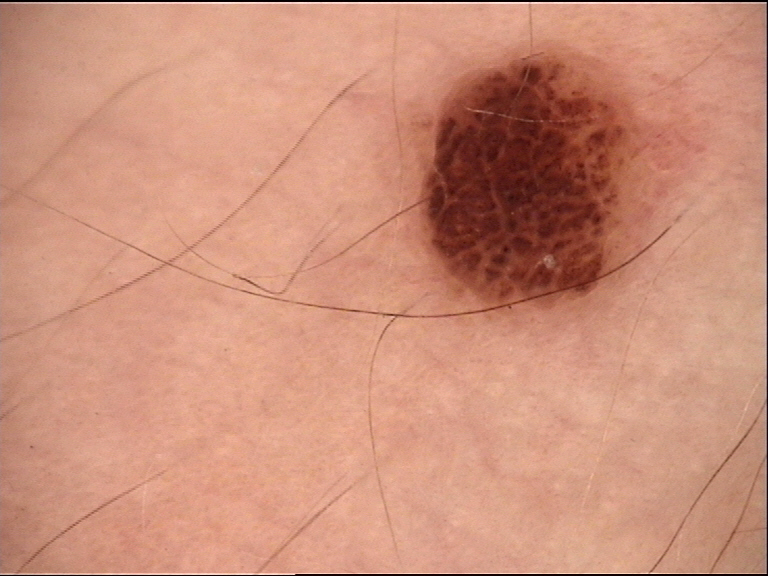<lesion>
  <diagnosis>
    <name>compound nevus</name>
    <code>cb</code>
    <malignancy>benign</malignancy>
    <super_class>melanocytic</super_class>
    <confirmation>expert consensus</confirmation>
  </diagnosis>
</lesion>